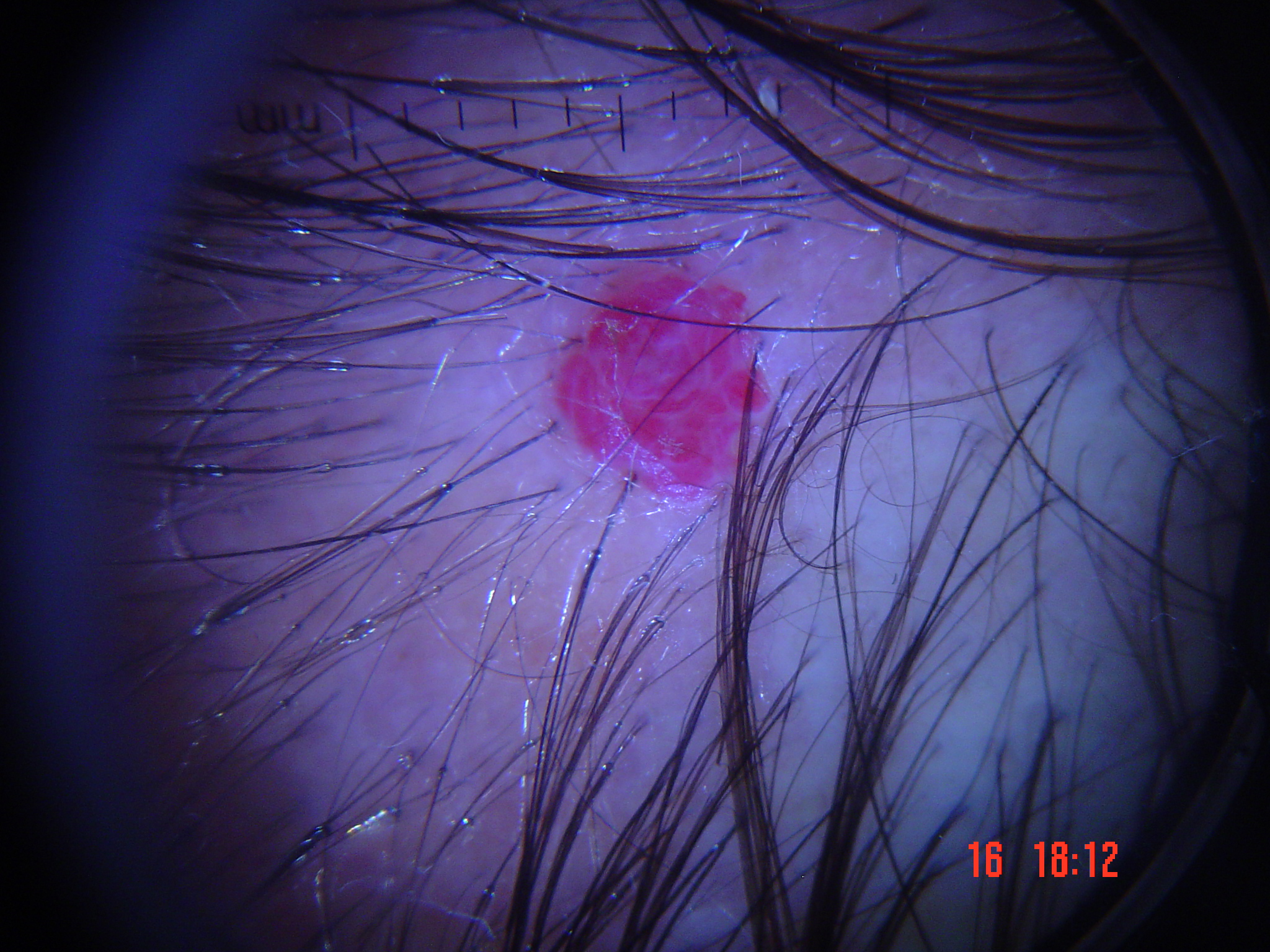Classified as a vascular lesion — a hemangioma.